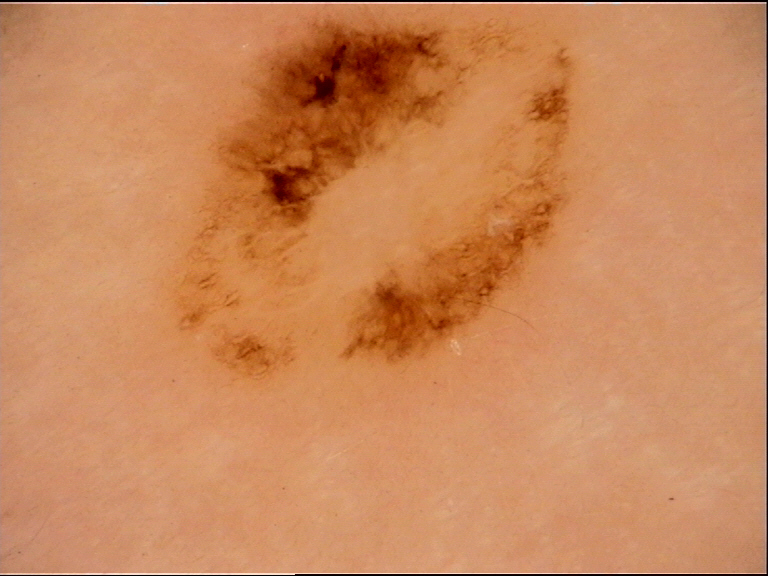A skin lesion imaged with a dermatoscope. Histopathology confirmed a melanoma.